A female subject aged 73-77 · Fitzpatrick skin type II:
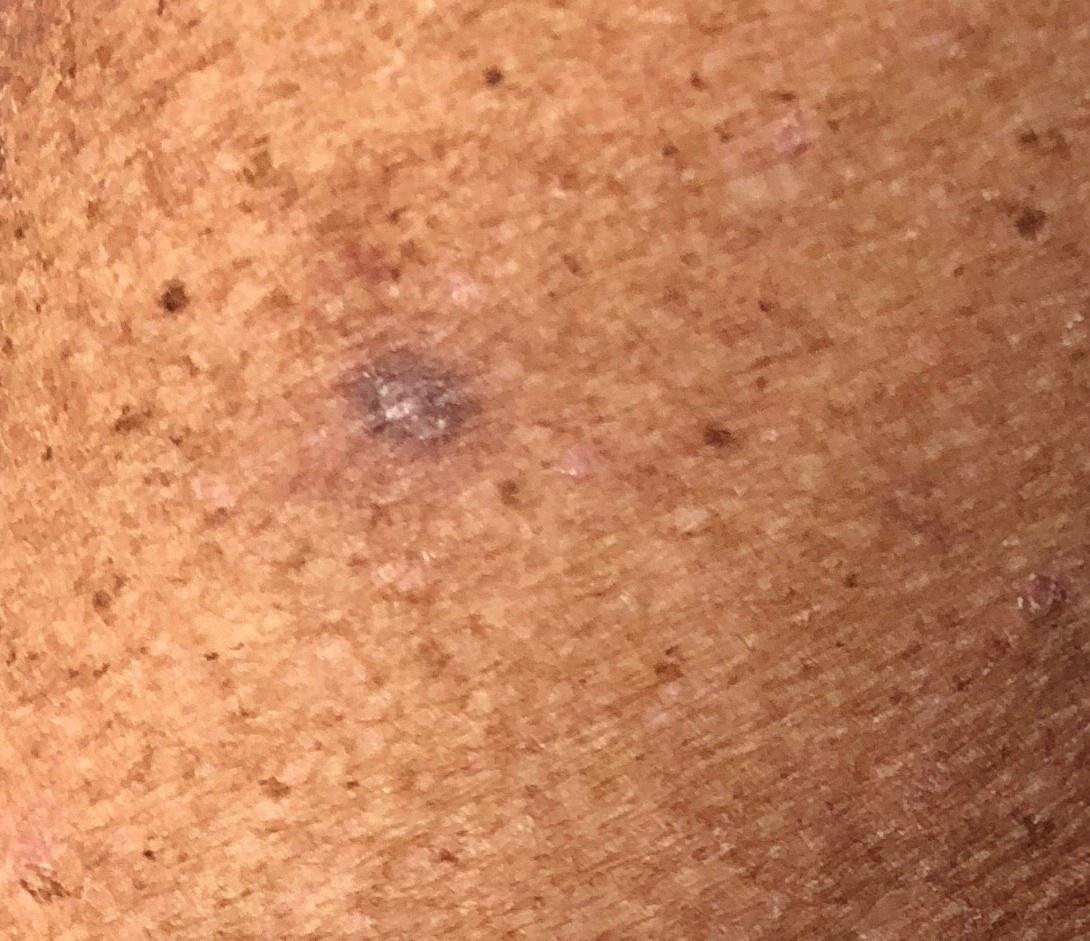The lesion is located on a lower extremity.
Histopathologically confirmed as a lesion of epidermal origin — a squamous cell carcinoma.